Located on the arm. This is a close-up image. Present for one to four weeks. FST II; lay reviewers estimated a Monk skin tone scale of 2: 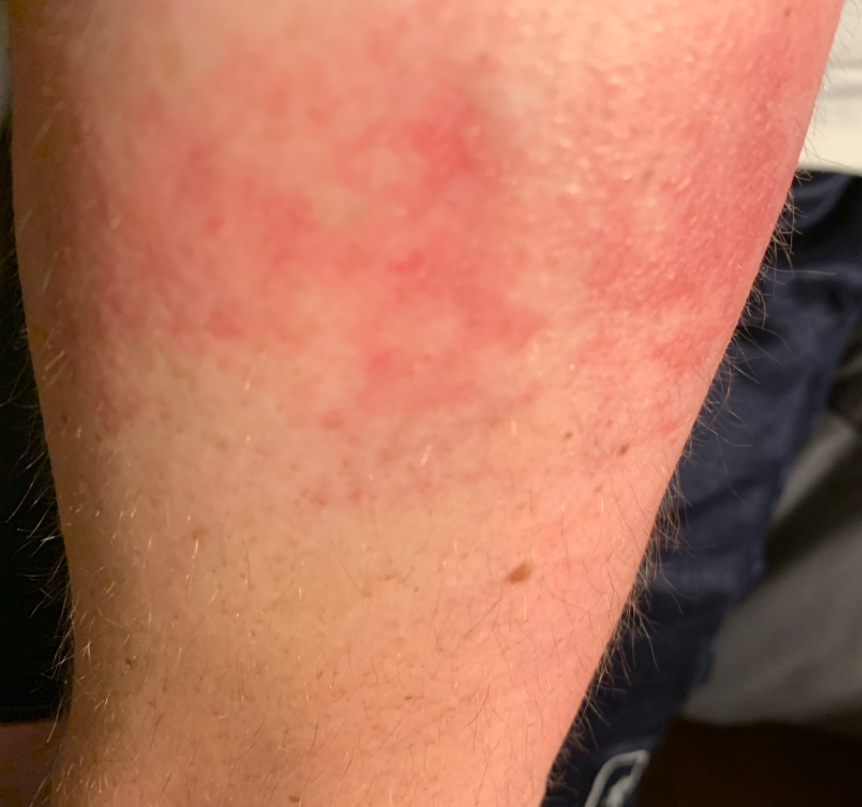Diagnostic features were not clearly distinguishable in this photograph.